This is a dermoscopic photograph of a skin lesion:
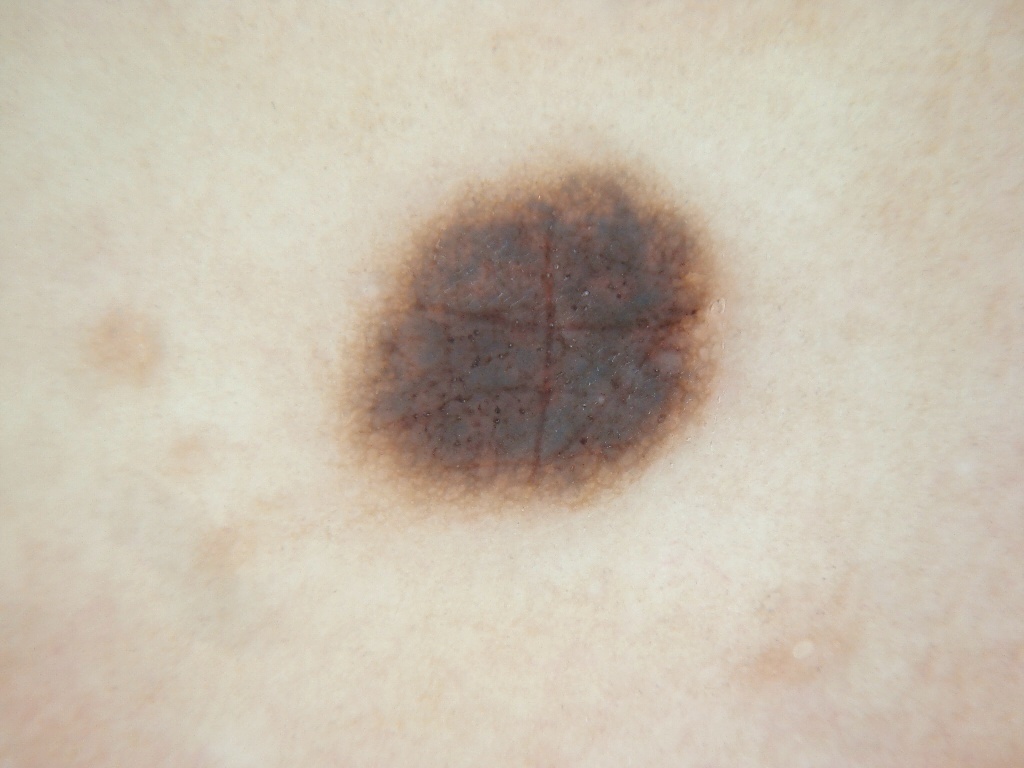– dermoscopic findings · pigment network; absent: globules, milia-like cysts, negative network, and streaks
– lesion bbox · [339,153,738,513]
– impression · a melanocytic nevus, a benign skin lesion